A dermatoscopic image of a skin lesion · a female patient 15 years old · referred for assessment of suspected melanocytic nevus — 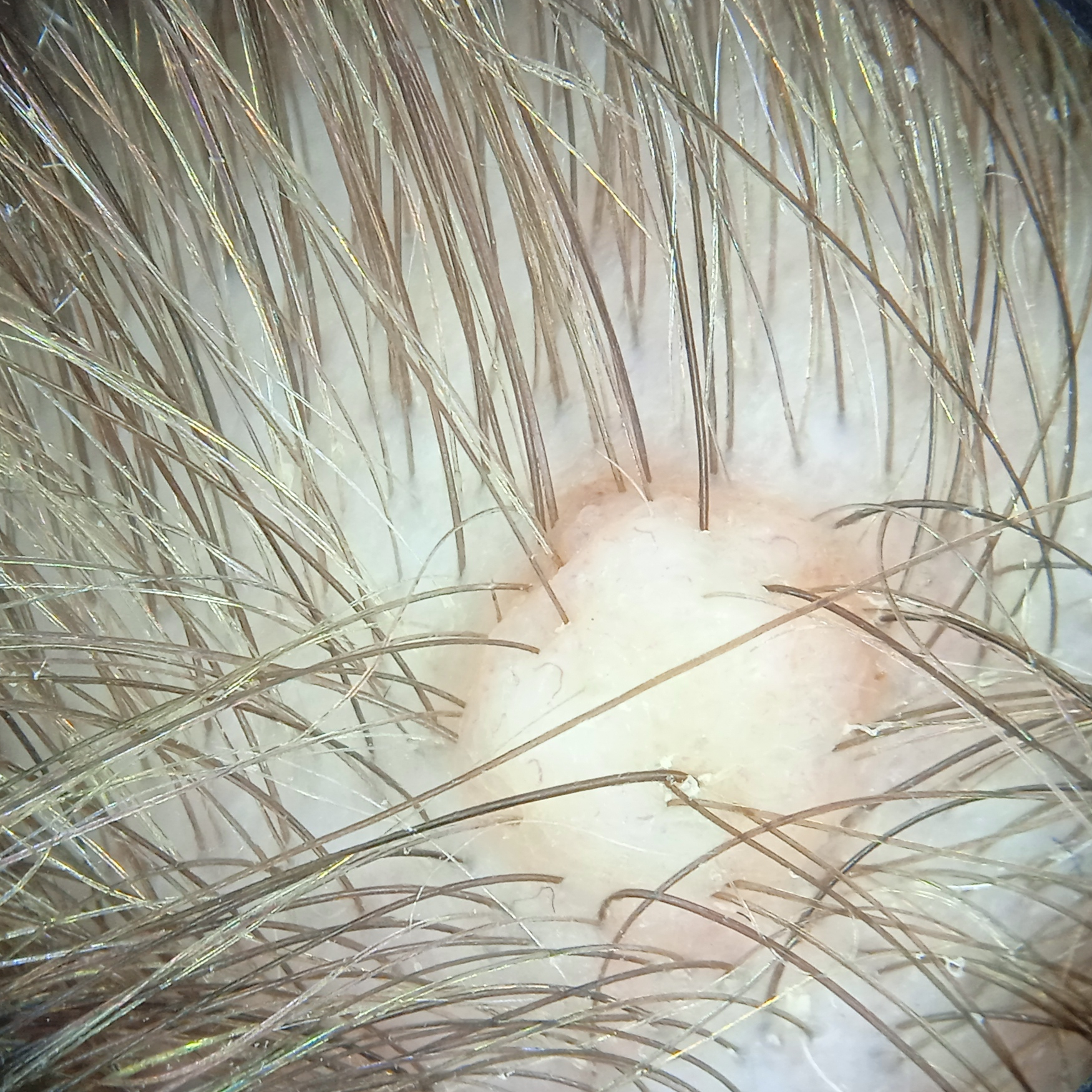diameter: 5 mm; diagnosis: melanocytic nevus (biopsy-proven).